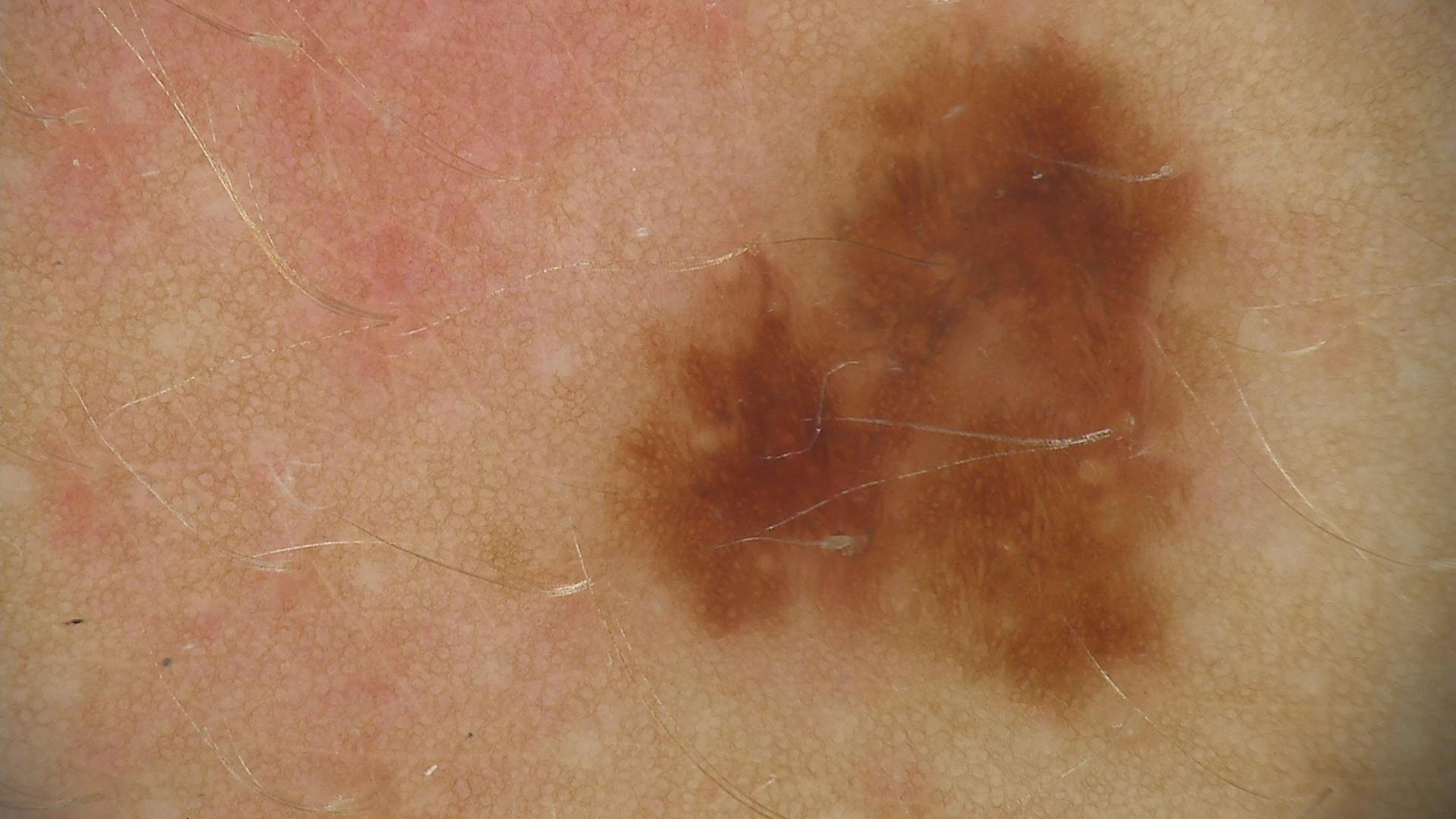Findings:
* image type · dermoscopy
* diagnosis · dysplastic junctional nevus (expert consensus)